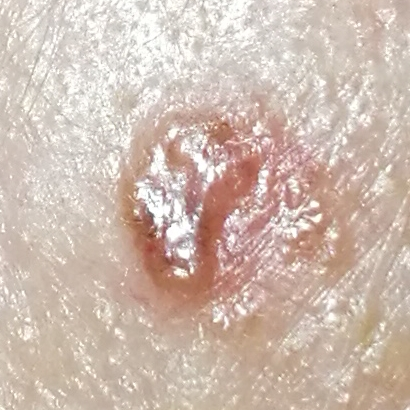Q: What are the relevant risk factors?
A: prior skin cancer (patient or family)
Q: Tell me about the patient.
A: female, in their early 80s
Q: What kind of image is this?
A: clinical photo
Q: What is the patient's skin type?
A: I
Q: What are the lesion's dimensions?
A: 4x4 mm
Q: What does the patient describe?
A: growth, elevation / no change in appearance
Q: What did the workup show?
A: basal cell carcinoma (biopsy-proven)